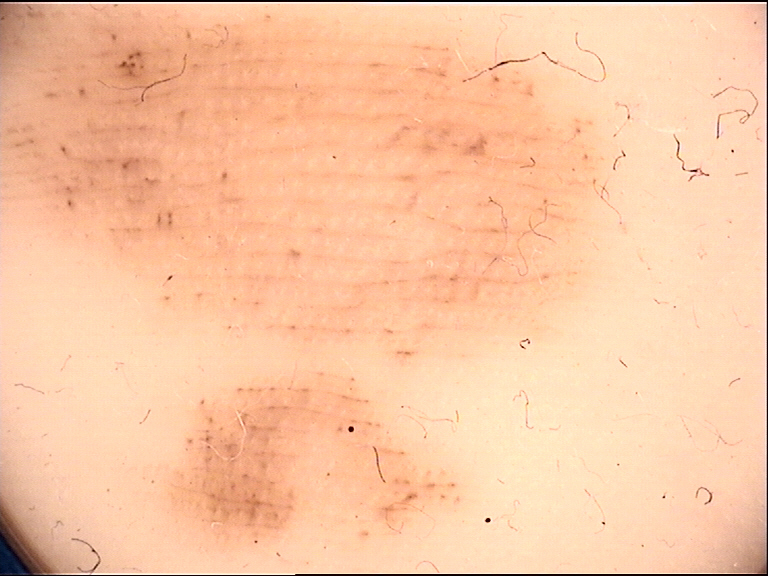Summary: Dermoscopy of a skin lesion. This is a banal lesion. Conclusion: The diagnosis was an acral junctional nevus.